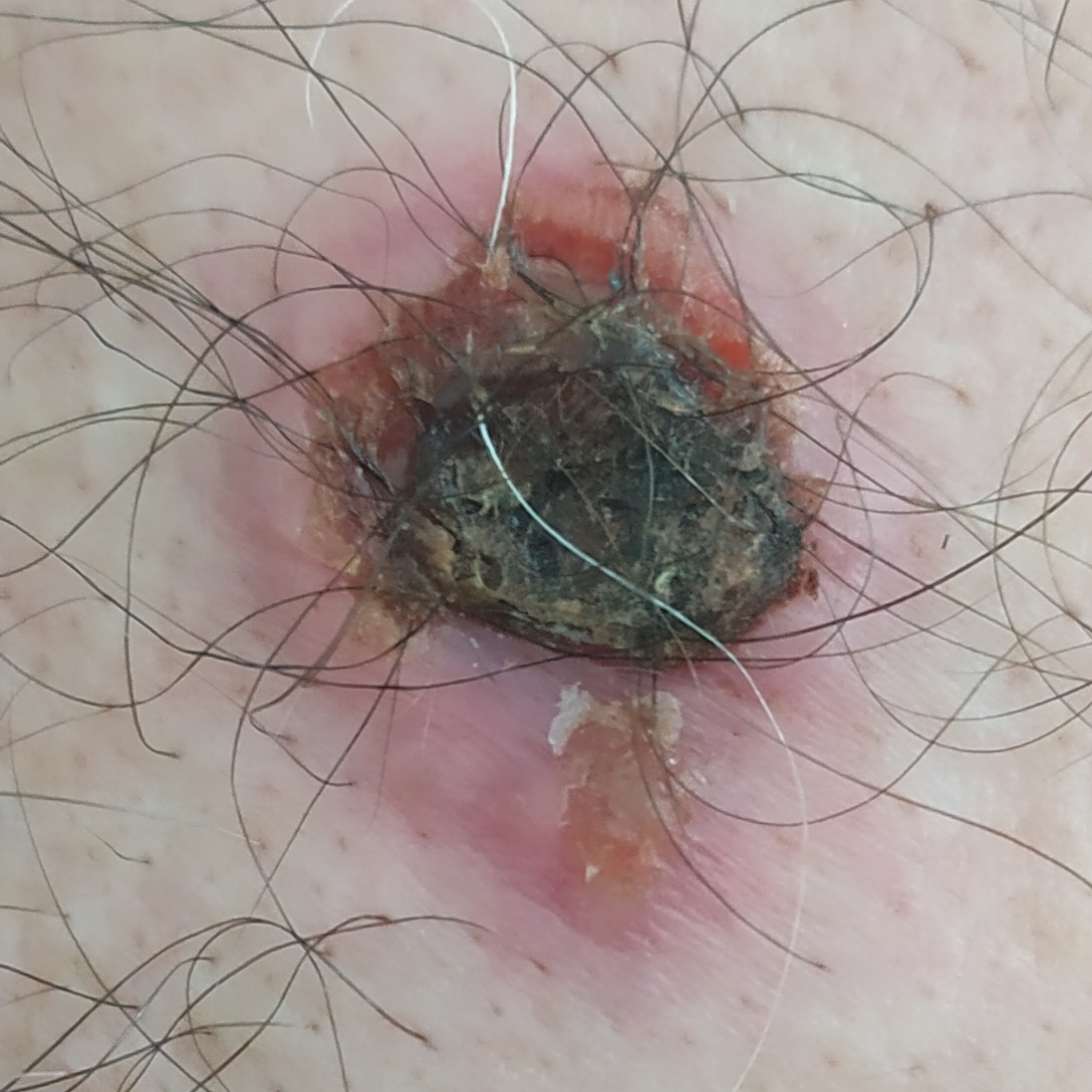Findings:
A male subject 40 years of age. A smartphone photograph of a skin lesion. The lesion was found on the chest. Per patient report, the lesion has bled, has grown, has changed, and is elevated.
Pathology:
The biopsy diagnosis was a basal cell carcinoma.